A dermoscopic close-up of a skin lesion.
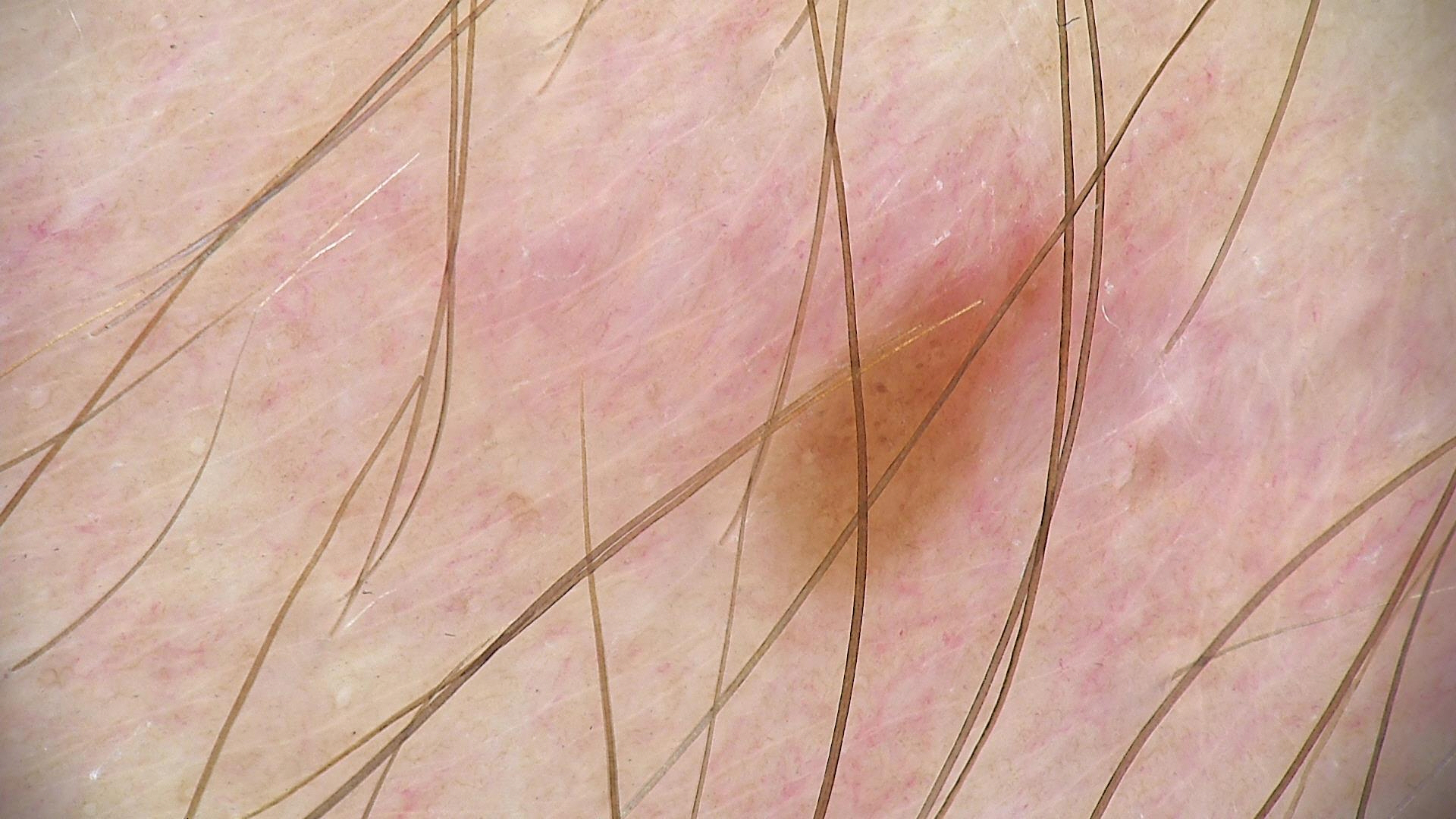lesion type — banal | label — junctional nevus (expert consensus).